The photo was captured at an angle, located on the top or side of the foot: 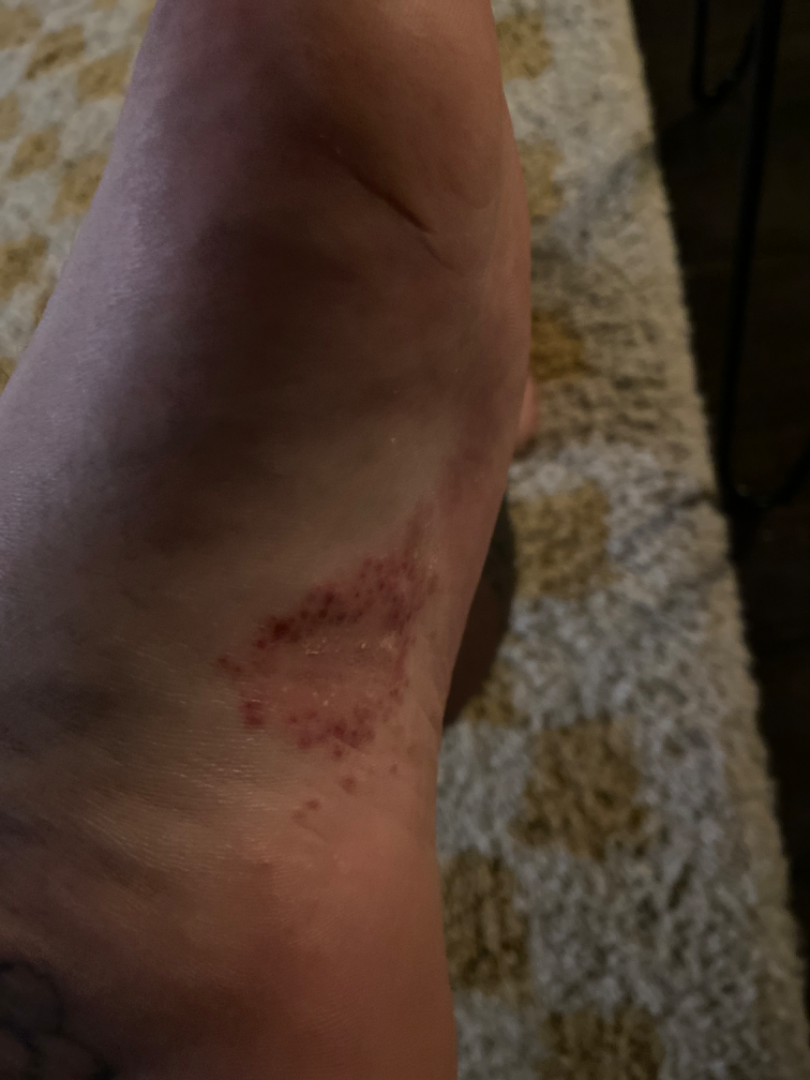symptoms = bothersome appearance
self-categorized as = a rash
texture = raised or bumpy
dermatologist impression = single-reviewer assessment: the leading consideration is Psoriasis; the differential also includes Tinea; less likely is Allergic Contact Dermatitis